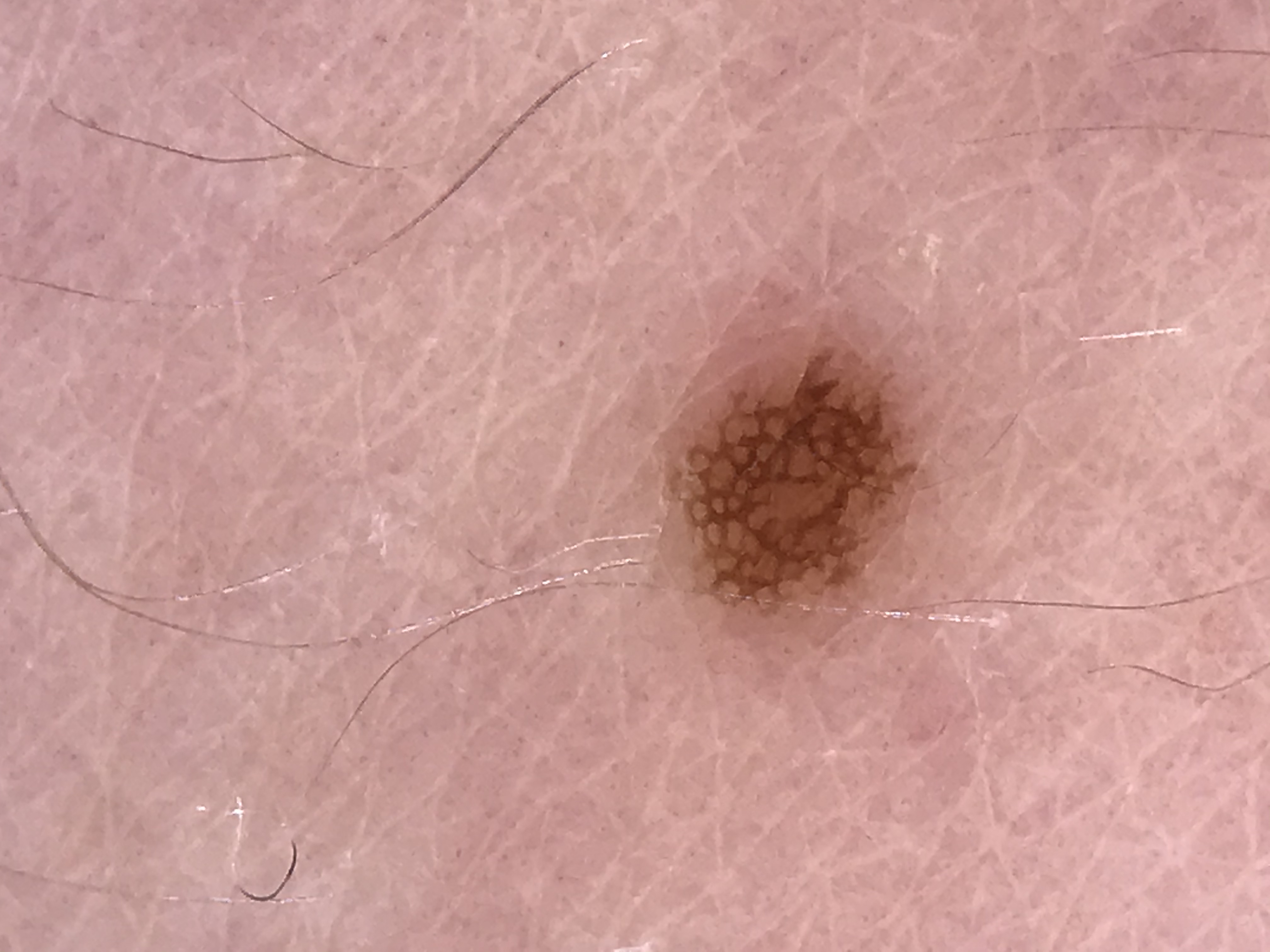label=junctional nevus (expert consensus).